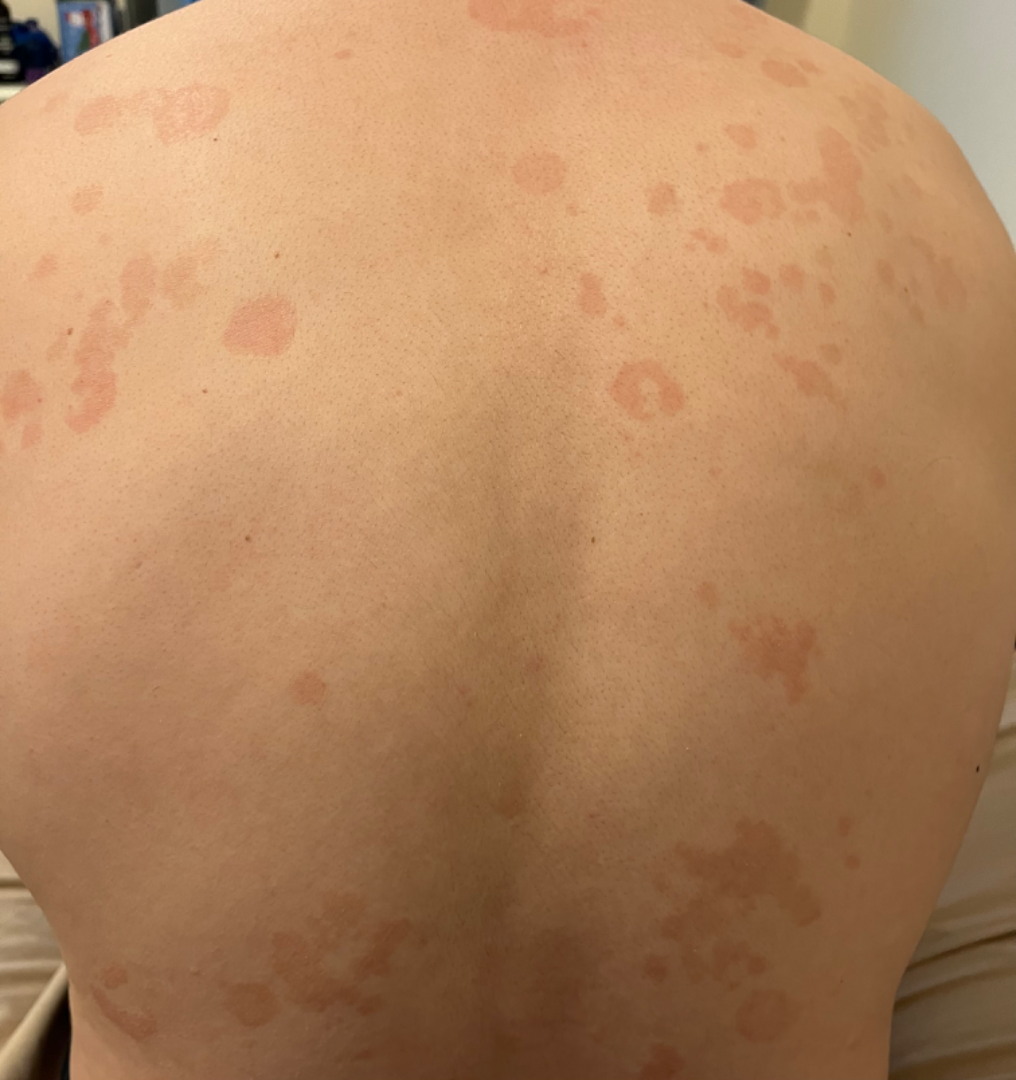clinical impression — consistent with Tinea Versicolor.